A clinical close-up photograph of a skin lesion · the patient was assessed as Fitzpatrick skin type II · the chart records alcohol use and no prior skin cancer (patient or family) · a female patient in their early 70s — 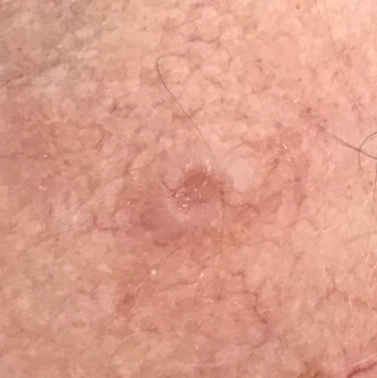Case:
– location · the face
– lesion diameter · approx. 7 × 5 mm
– patient-reported symptoms · growth, itching, elevation
– diagnostic label · basal cell carcinoma (biopsy-proven)